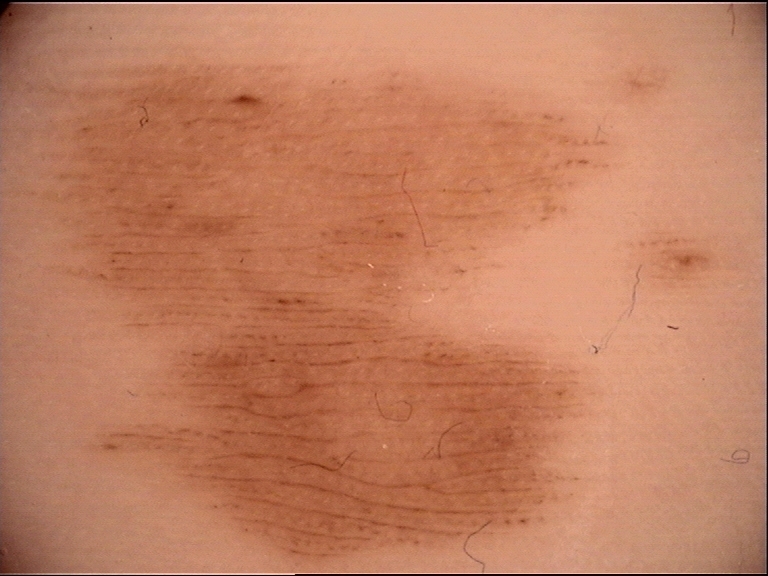The diagnosis was an acral junctional nevus.